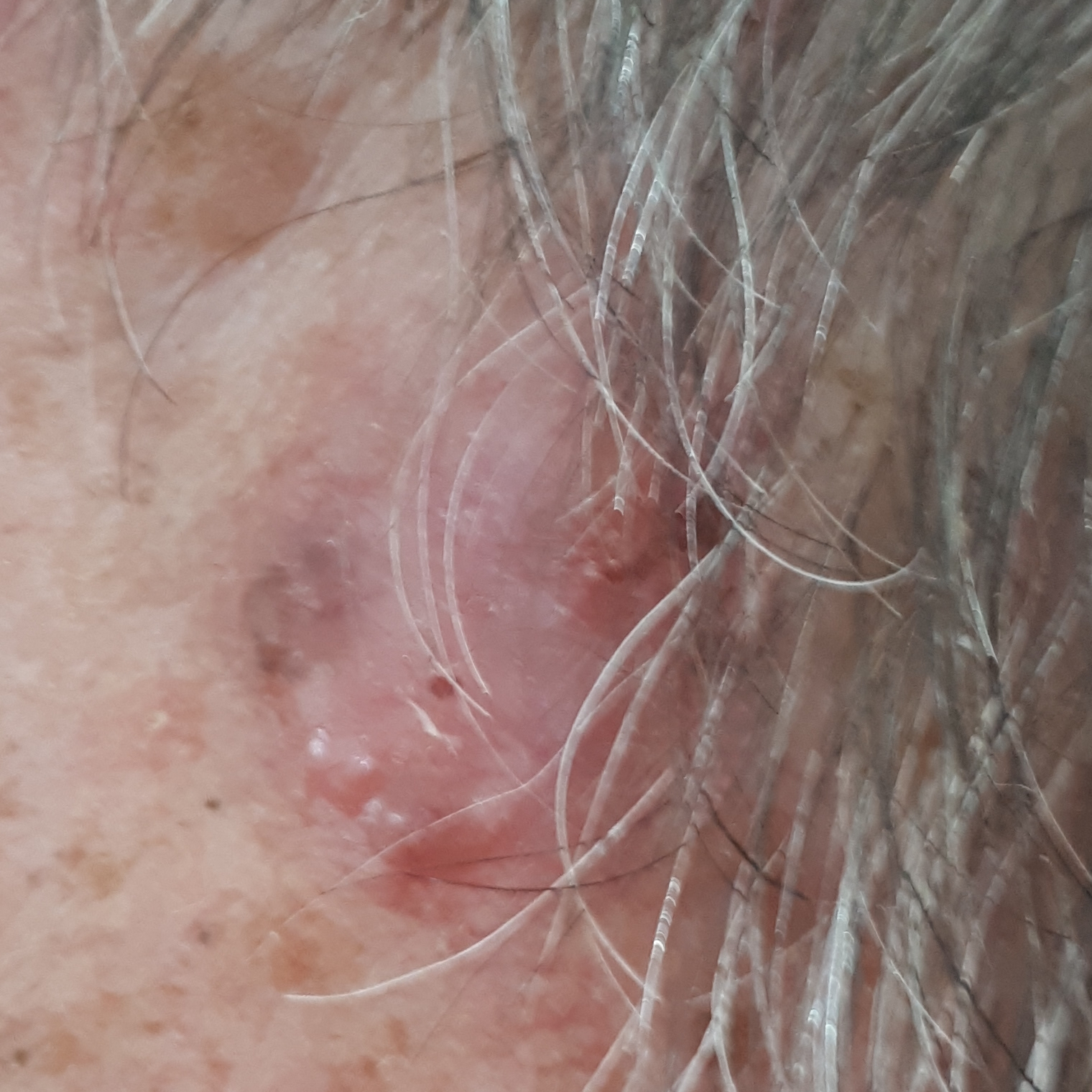A male subject 77 years of age. A clinical photograph of a skin lesion. The lesion is on the face. The patient reports that the lesion is elevated and itches. Histopathological examination showed a basal cell carcinoma.